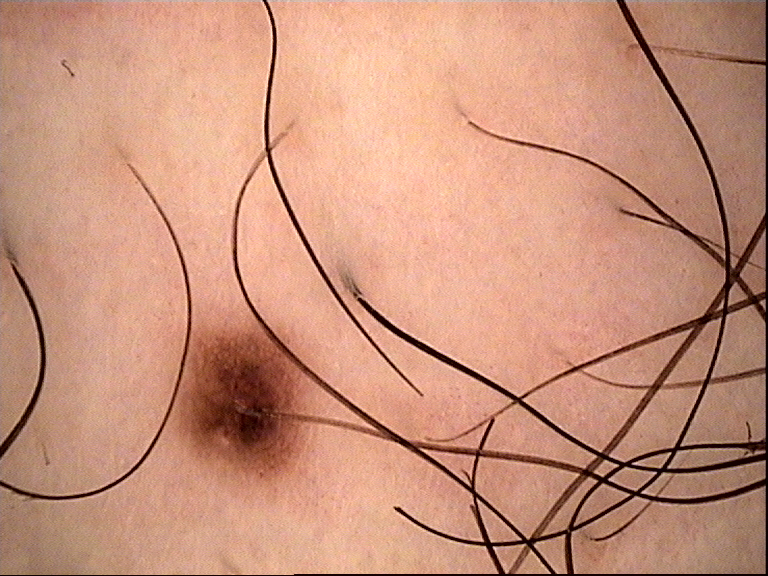class = dysplastic junctional nevus (expert consensus).